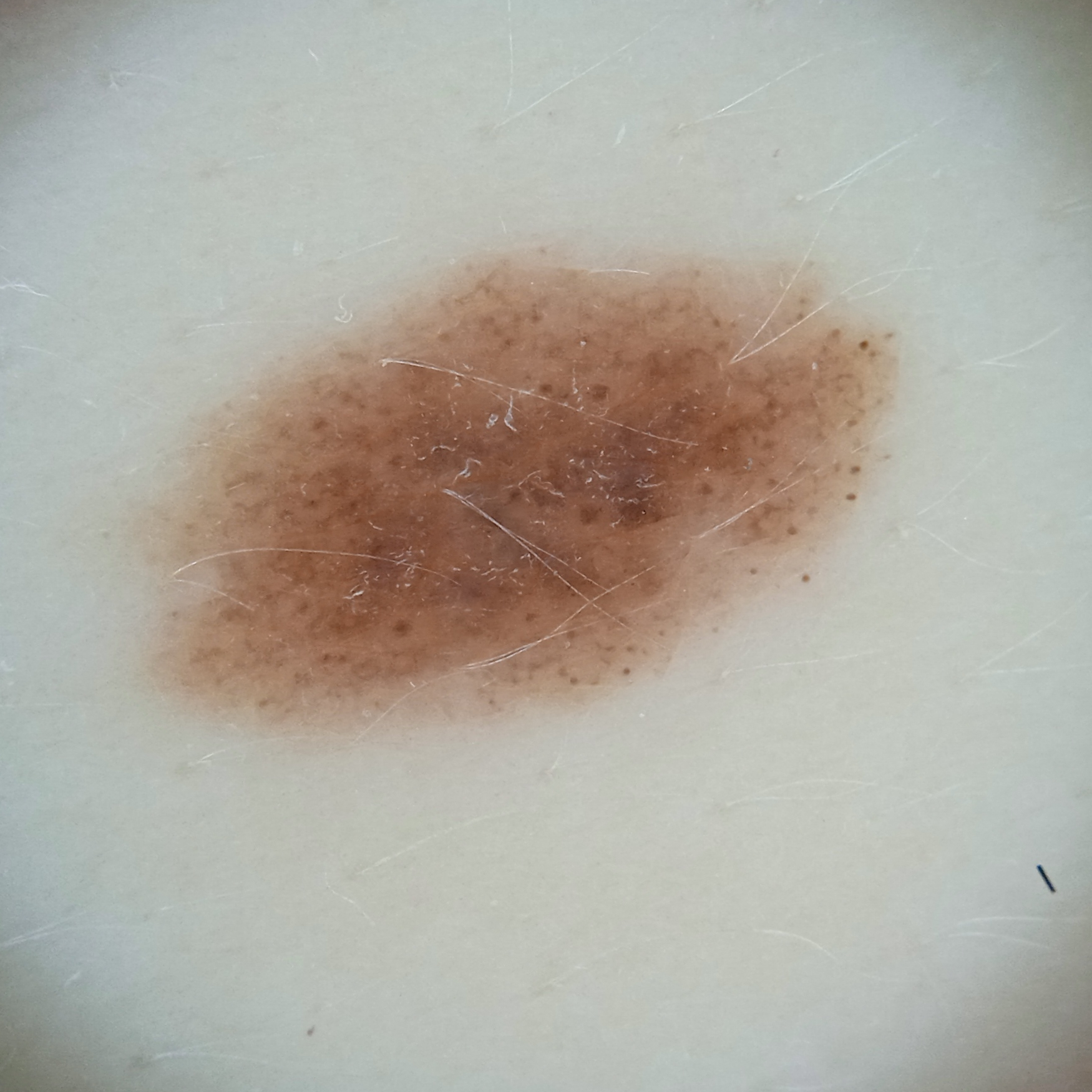Imaged for a research study, with no referral diagnosis recorded.
A female patient 27 years of age.
A skin lesion imaged with a dermatoscope.
Located on the back.
Measuring roughly 9.4 mm.
The lesion was assessed as a melanocytic nevus.